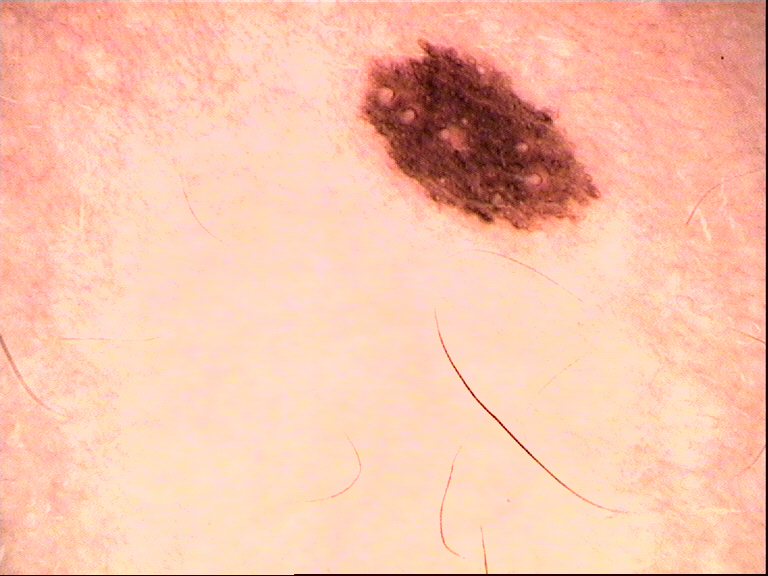Conclusion:
The diagnostic label was a dysplastic junctional nevus.